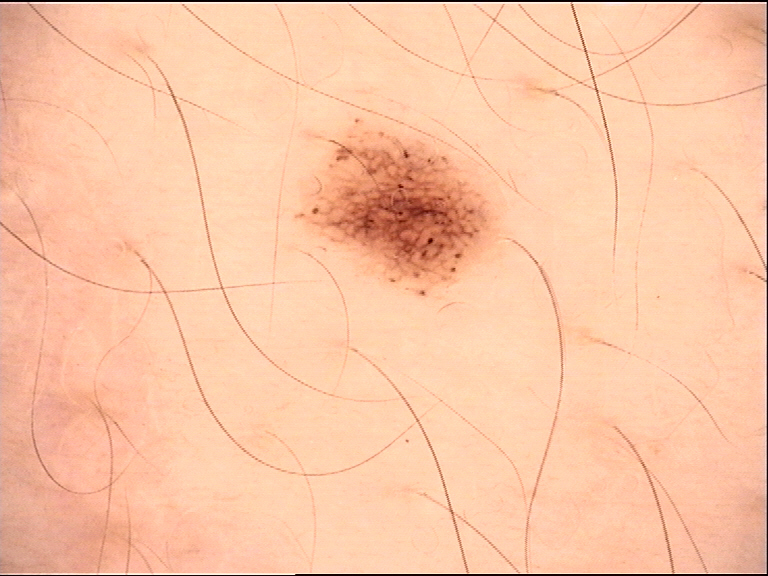A dermoscopic photograph of a skin lesion. The diagnosis was a benign lesion — a dysplastic junctional nevus.